The lesion involves the back of the torso, leg, front of the torso and arm. The patient notes associated fatigue, chills and joint pain. The patient described the issue as a rash. An image taken at an angle. The condition has been present for one to four weeks:
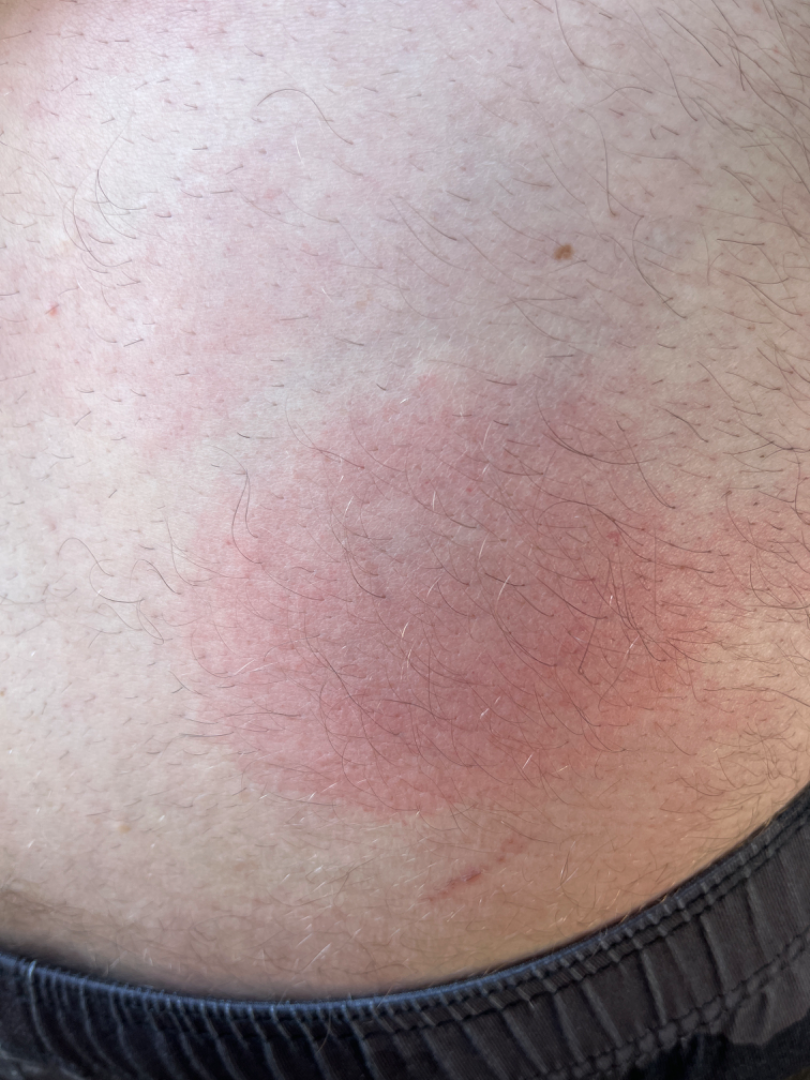Assessment: Diagnostic features were not clearly distinguishable in this photograph.